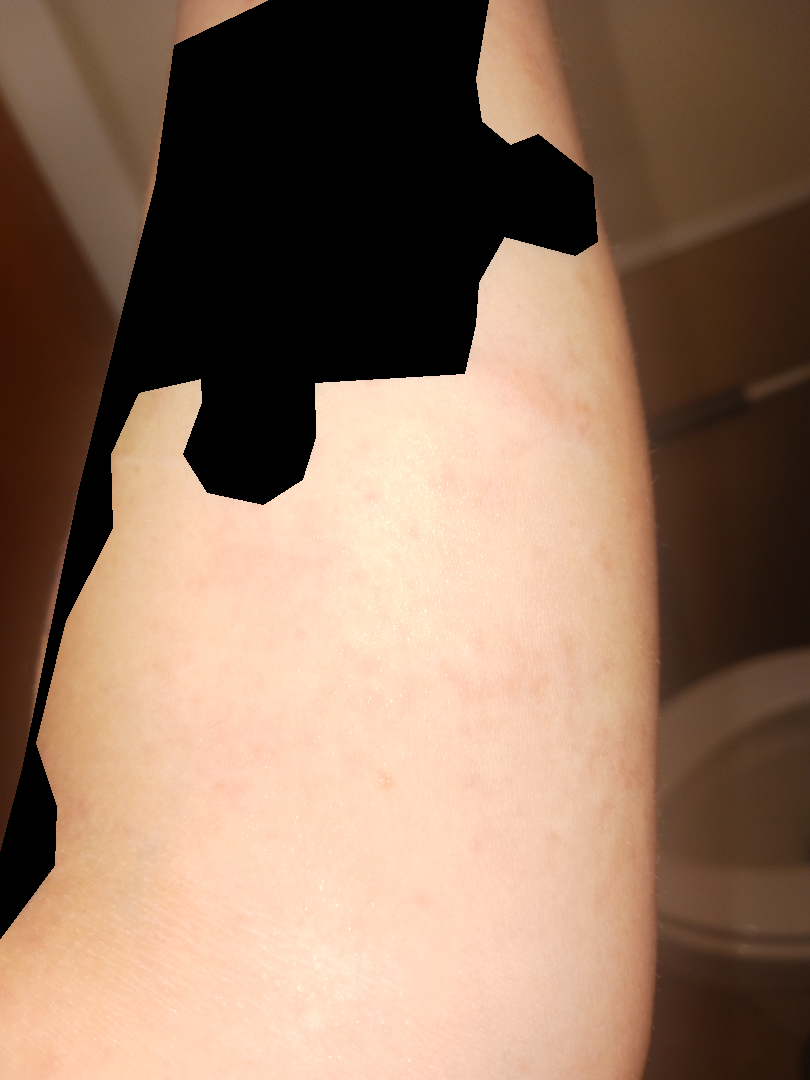<dermatology_case>
  <assessment>ungradable on photographic review</assessment>
</dermatology_case>